The patient describes having few moles overall · acquired for a research image collection, with no referral diagnosis · a female patient 48 years of age · the patient says their skin reddens painfully with sun exposure · a dermoscopic image of a skin lesion · by self-report, a family history of skin cancer and a history of sunbed use.
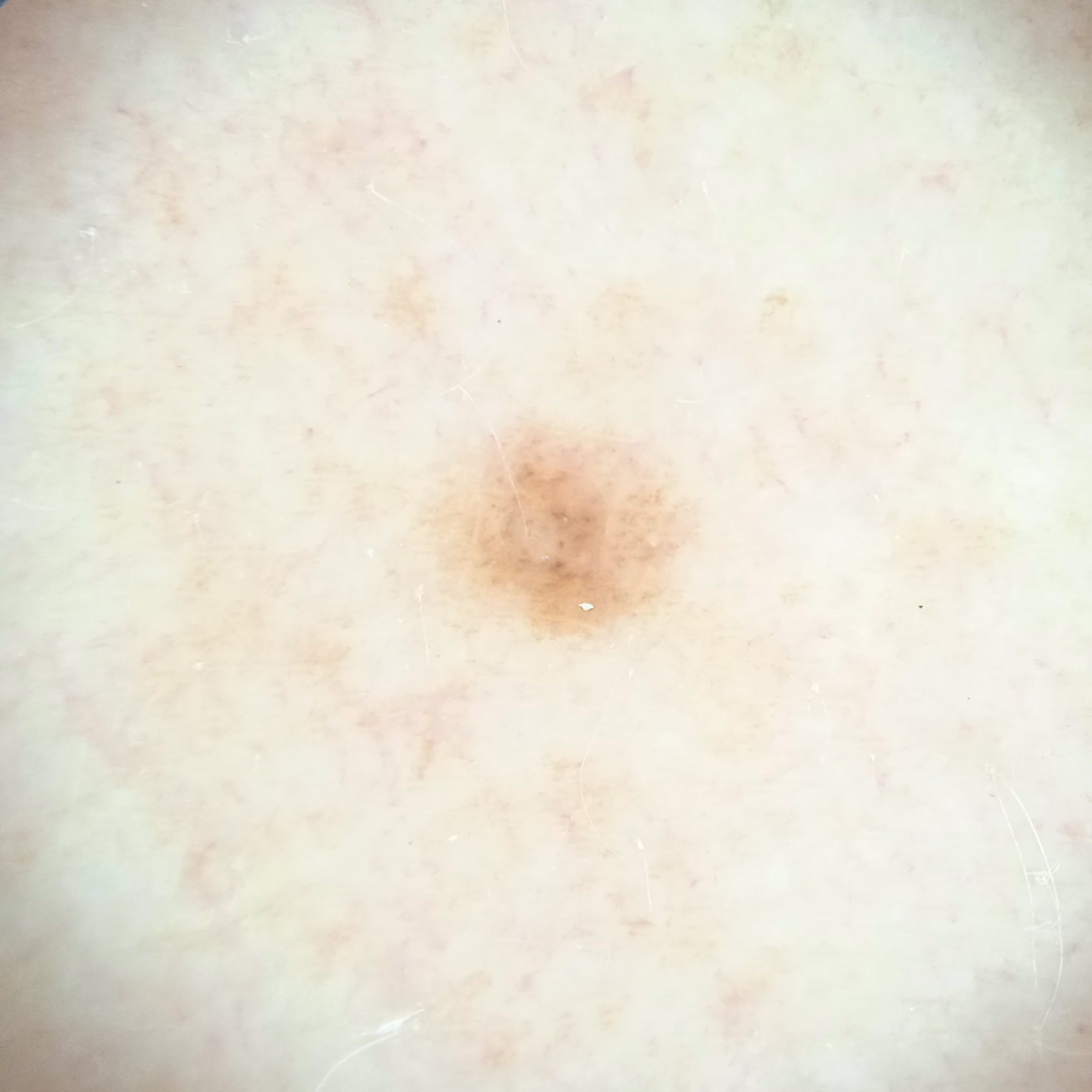Clinical context:
The lesion is on an arm. Measuring roughly 2.7 mm.
Impression:
The consensus diagnosis for this lesion was a melanocytic nevus.